Located on the leg. The contributor is a female aged 18–29. An image taken at a distance: 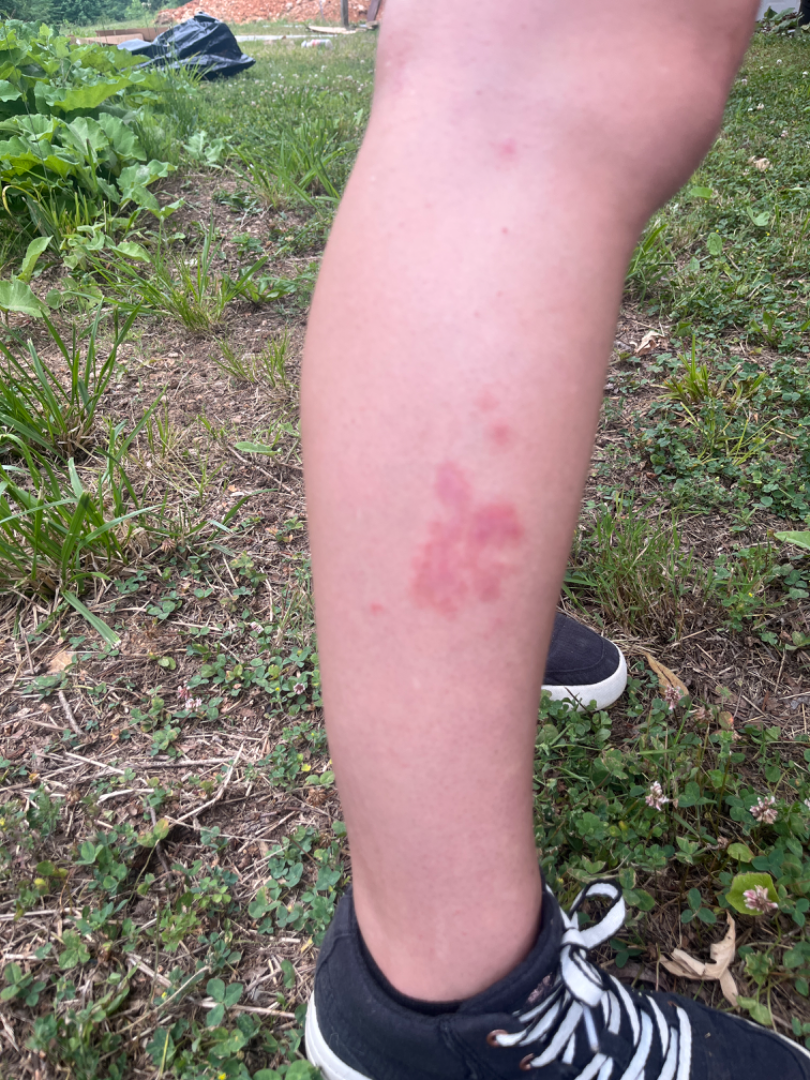skin tone = Fitzpatrick skin type II; lay reviewers estimated a Monk Skin Tone of 2, constitutional symptoms = mouth sores and fatigue, lesion texture = rough or flaky and flat, history = three to twelve months, patient-reported symptoms = itching, assessment = most likely Allergic Contact Dermatitis; possibly Insect Bite; lower on the differential is Eczema.